A female patient in their 70s · a skin lesion imaged with contact-polarized dermoscopy.
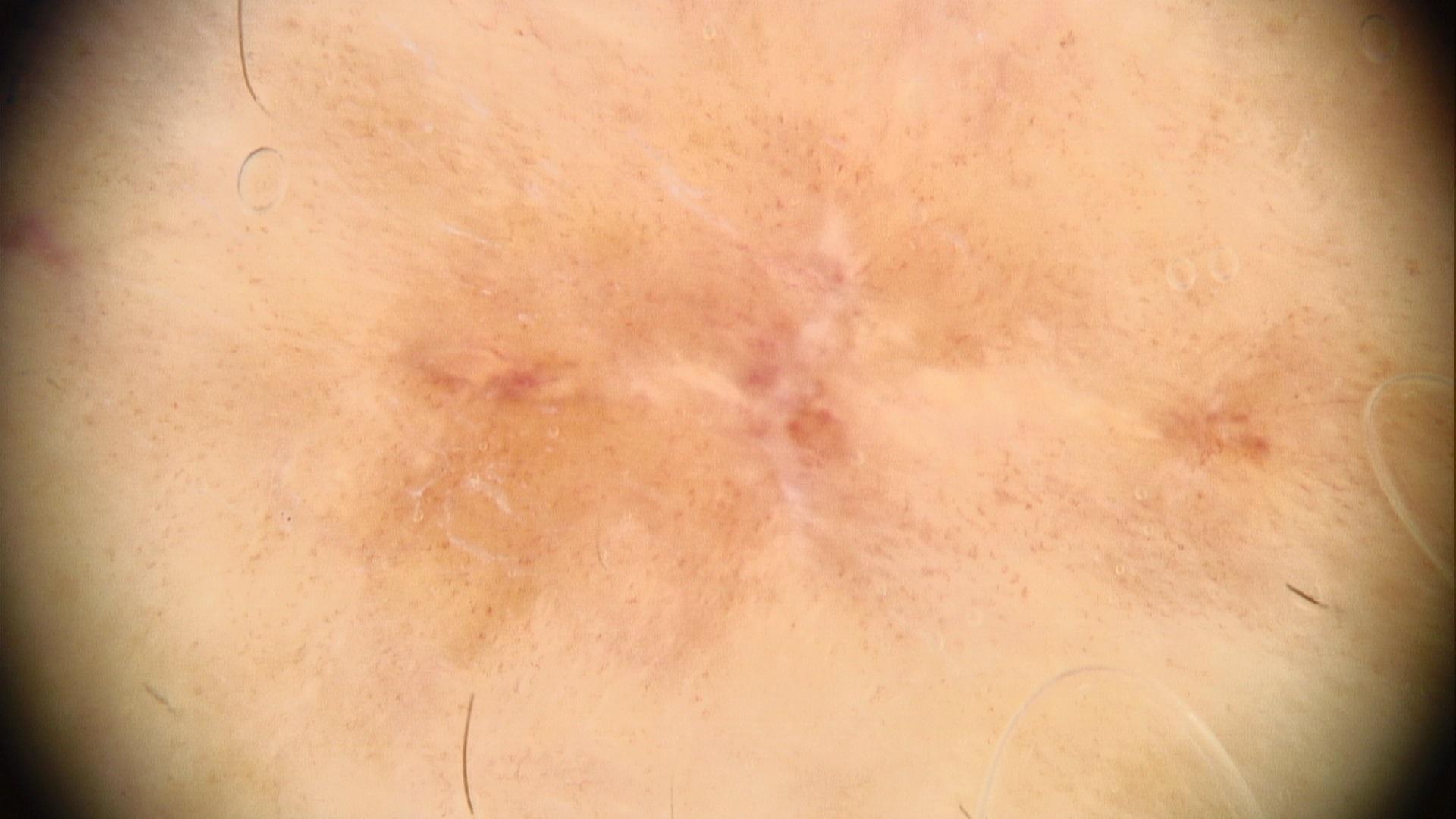The lesion involves a lower extremity. Histopathologically confirmed as a lesion of epidermal origin — a solar or actinic keratosis.